A dermoscopic photograph of a skin lesion.
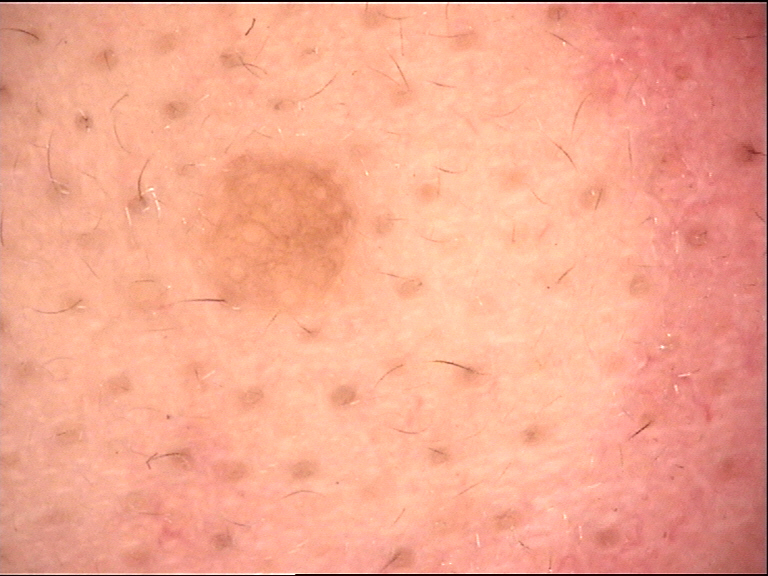Findings: This is a banal lesion. Conclusion: Labeled as a dermal nevus.